This image was taken at an angle · present for three to twelve months · the contributor is 18–29, female · self-categorized by the patient as a rash · the lesion is associated with itching, burning and darkening · the affected area is the arm:
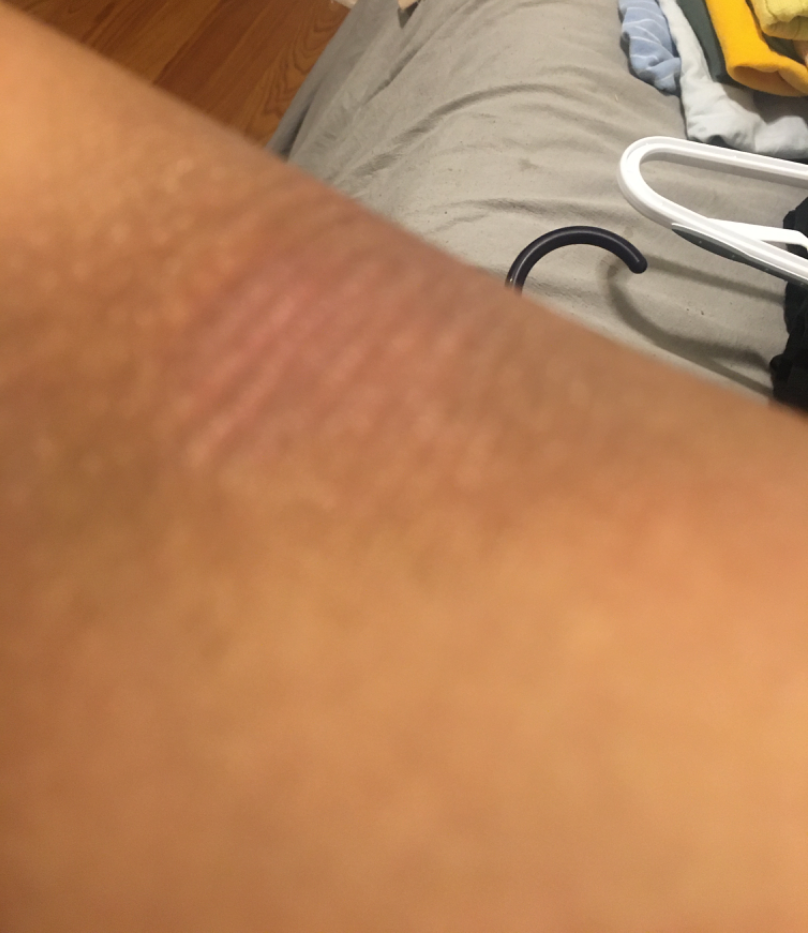A single dermatologist reviewed the case: Lichen Simplex Chronicus, Lichen planus/lichenoid eruption and Eczema were each considered, in no particular order.